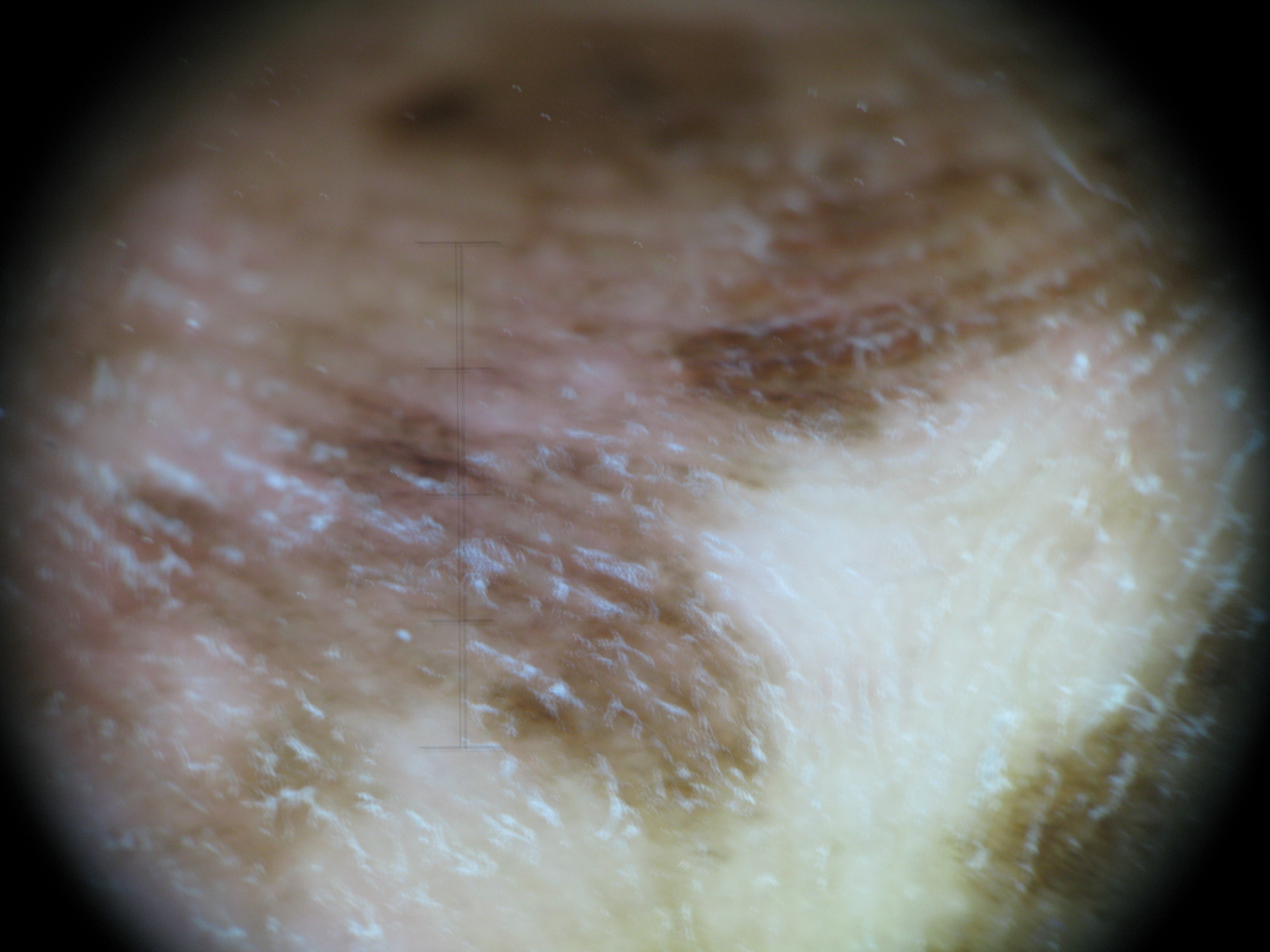{
  "diagnosis": {
    "name": "acral lentiginous melanoma",
    "code": "alm",
    "malignancy": "malignant",
    "super_class": "melanocytic",
    "confirmation": "histopathology"
  }
}